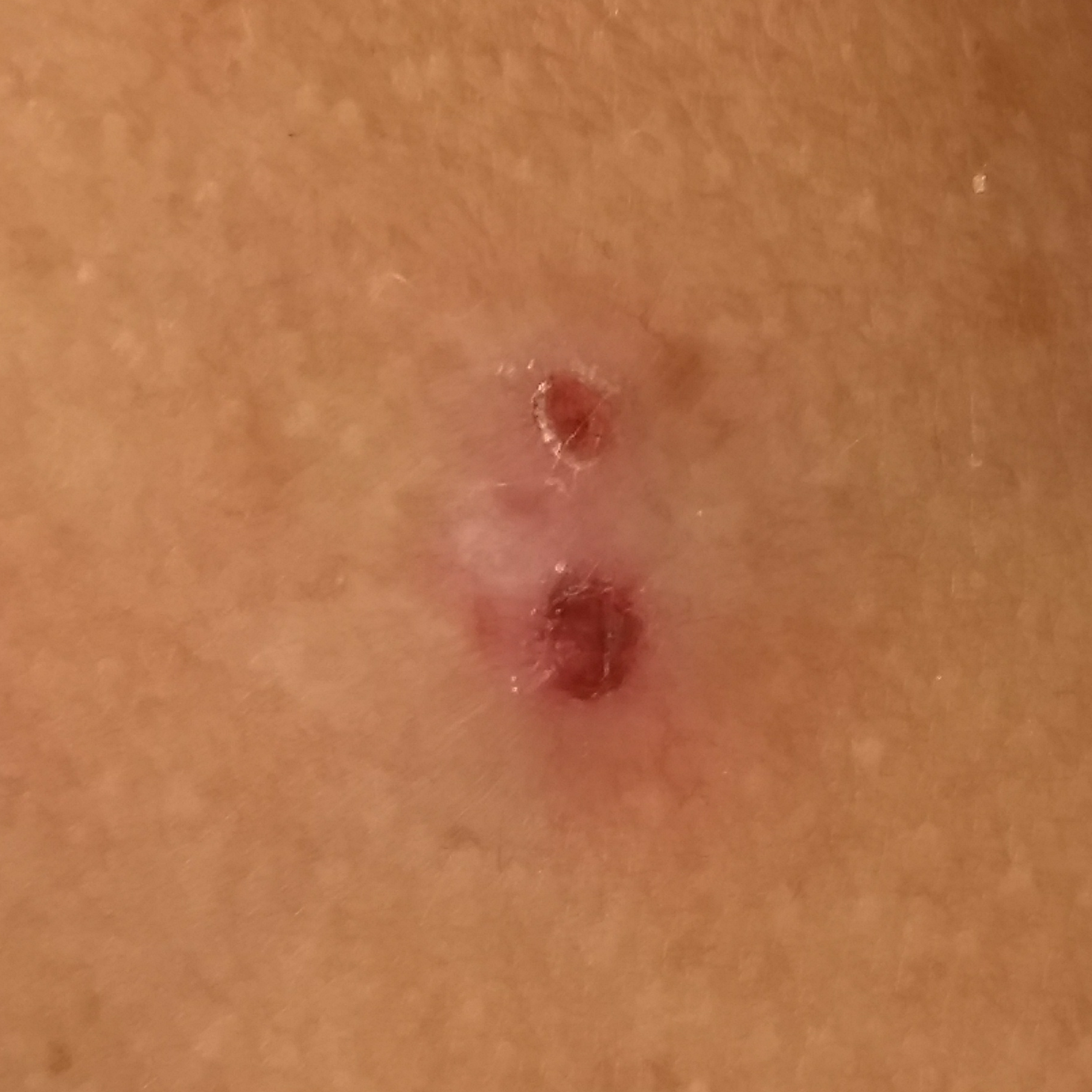Case summary:
The chart records prior skin cancer (patient or family), prior malignancy (patient or family), and pesticide exposure. A female subject 26 years of age. The patient is FST III. A clinical photograph showing a skin lesion. The lesion involves the chest. Measuring about 9 × 6 mm. By the patient's account, the lesion itches, is elevated, has bled, and hurts, but has not changed and has not grown.
Conclusion:
Confirmed on histopathology as a malignancy — a basal cell carcinoma.